Close-up view — 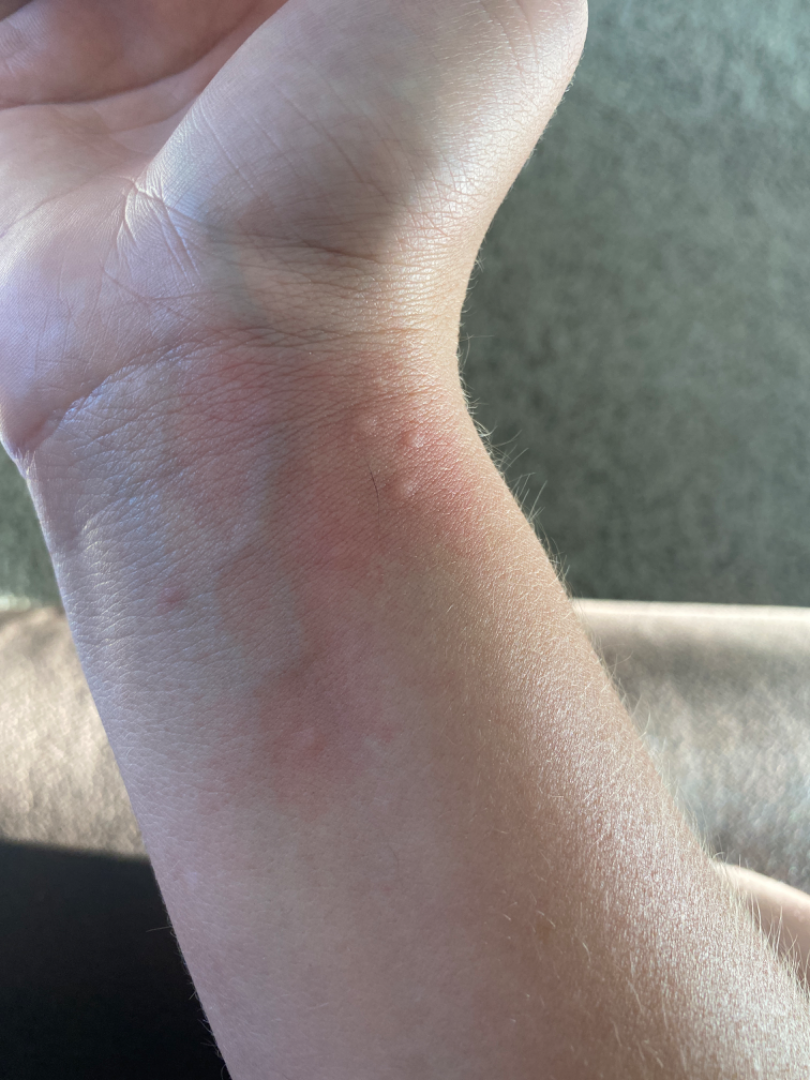dermatologist impression: favoring Insect Bite; also raised was Urticaria.